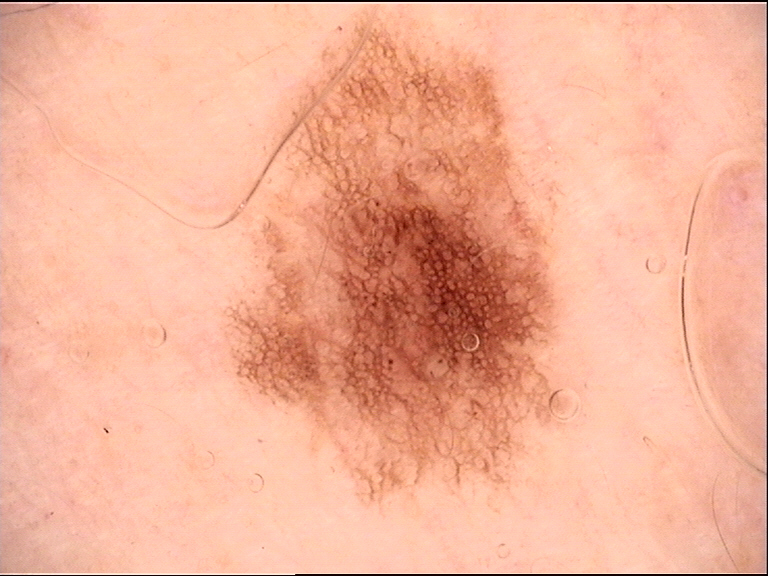assessment: dysplastic junctional nevus (expert consensus)